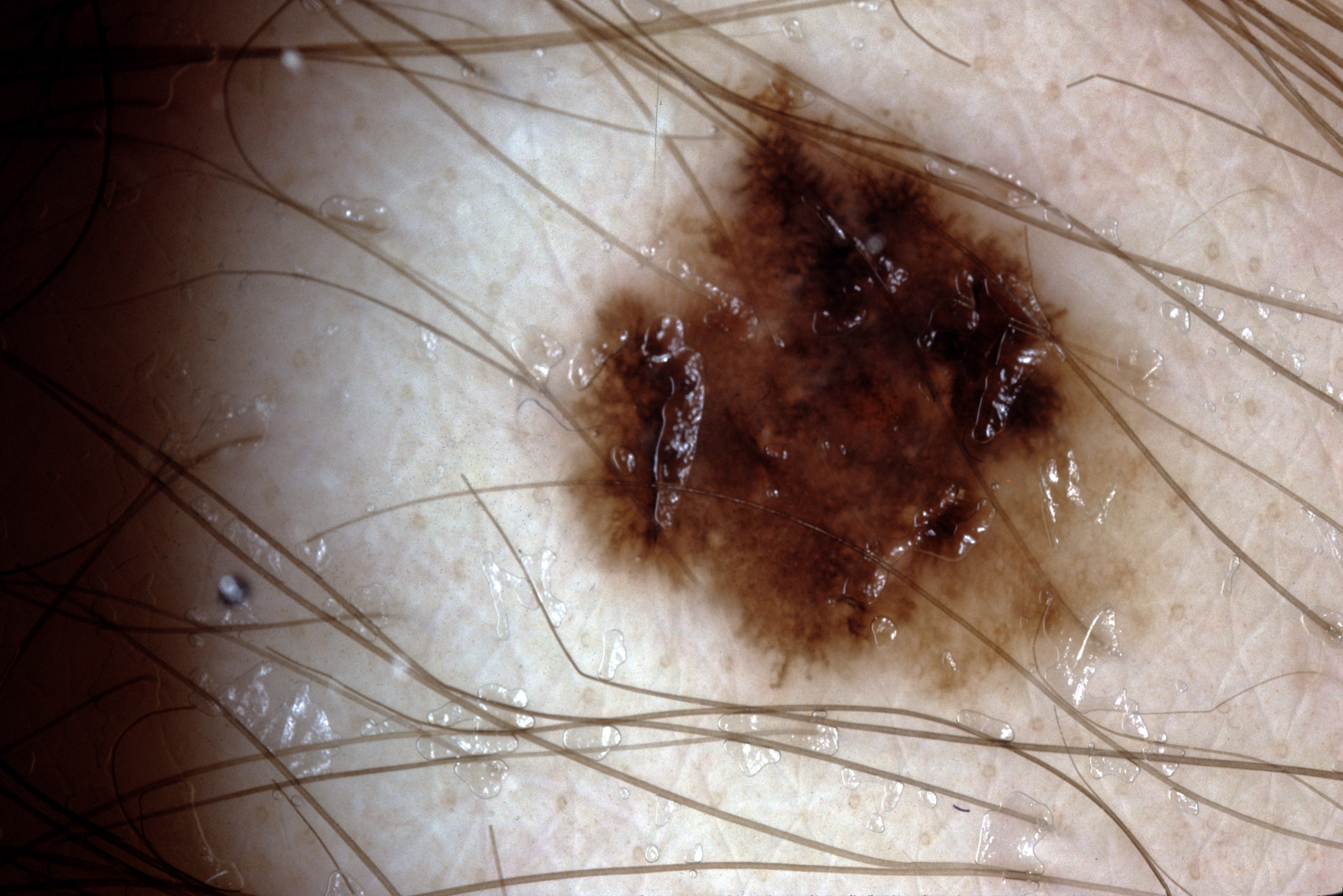Findings:
• imaging — dermoscopic image
• dermoscopic features — streaks and pigment network; absent: negative network and milia-like cysts
• lesion bbox — [549, 51, 1203, 711]
• assessment — a melanoma, a malignant skin lesion